A dermoscopic image of a skin lesion.
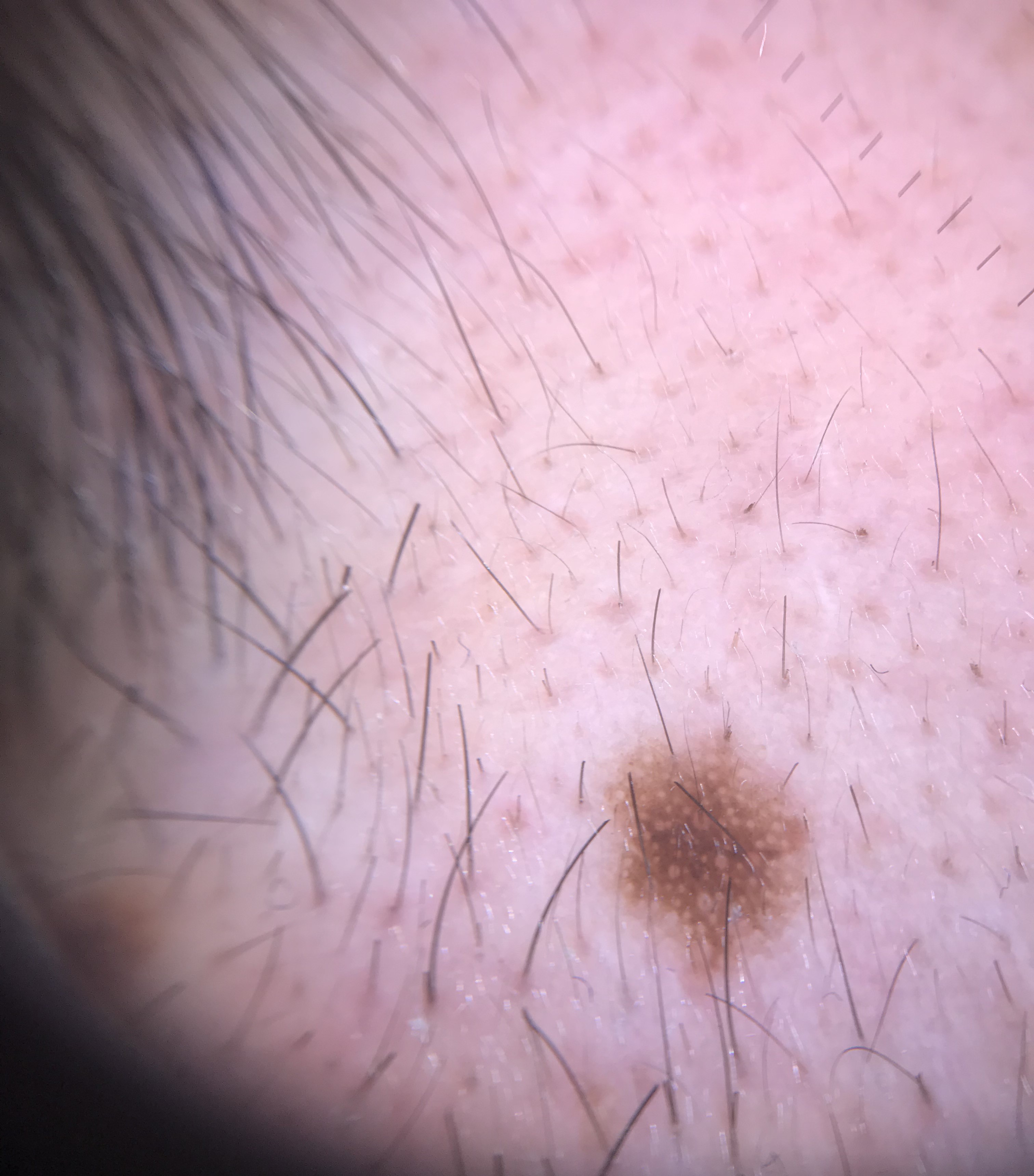label=Miescher nevus (expert consensus).